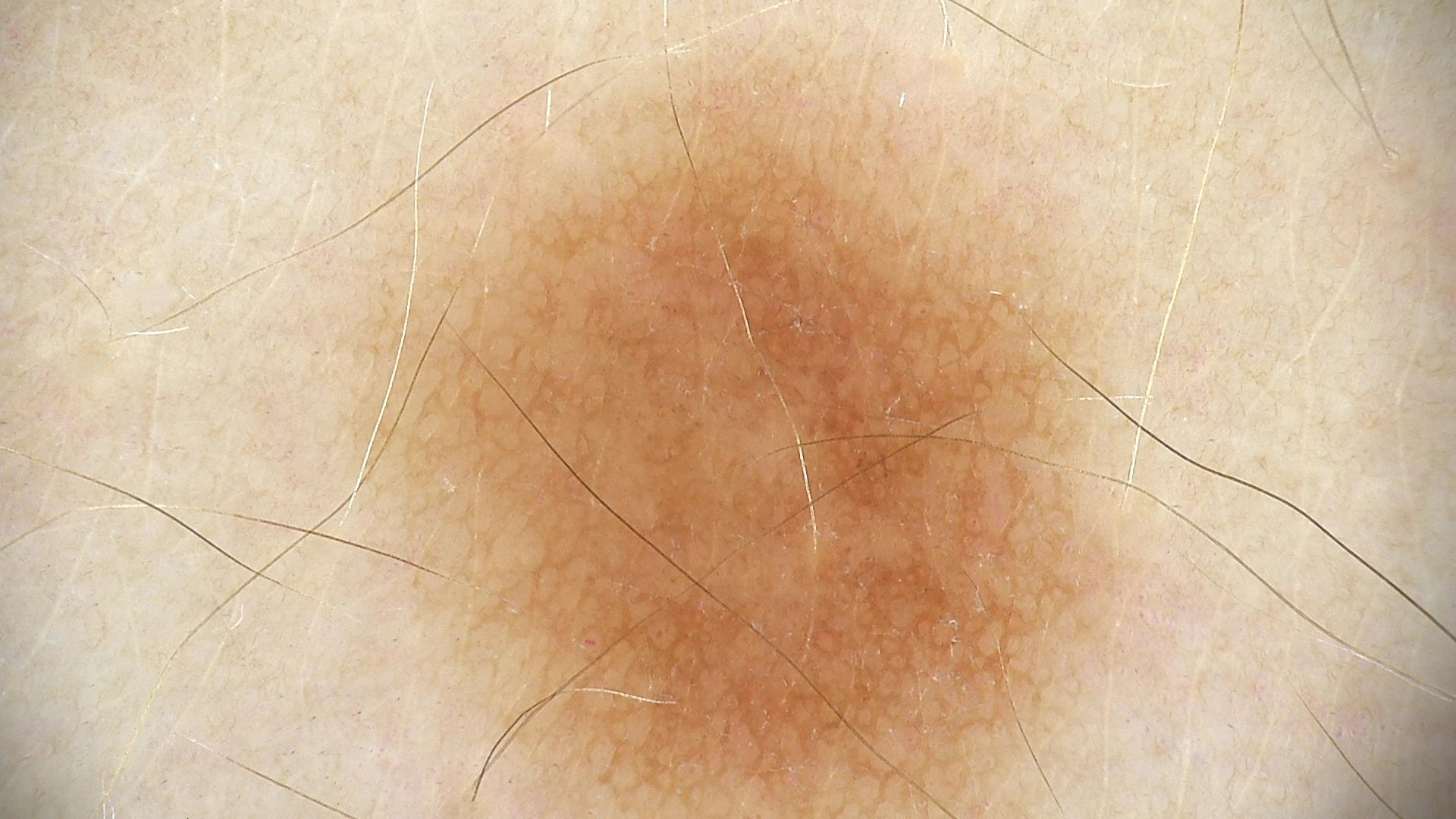The morphology is that of a banal lesion.
The diagnosis was a junctional nevus.